A clinical photo of a skin lesion taken with a smartphone — 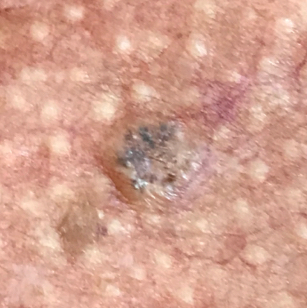Clinical context:
Located on the chest. By the patient's account, the lesion has grown and is elevated.
Conclusion:
The diagnostic impression was a seborrheic keratosis.